The leg and top or side of the foot are involved · the patient is a female aged 50–59 · the photograph is a close-up of the affected area: 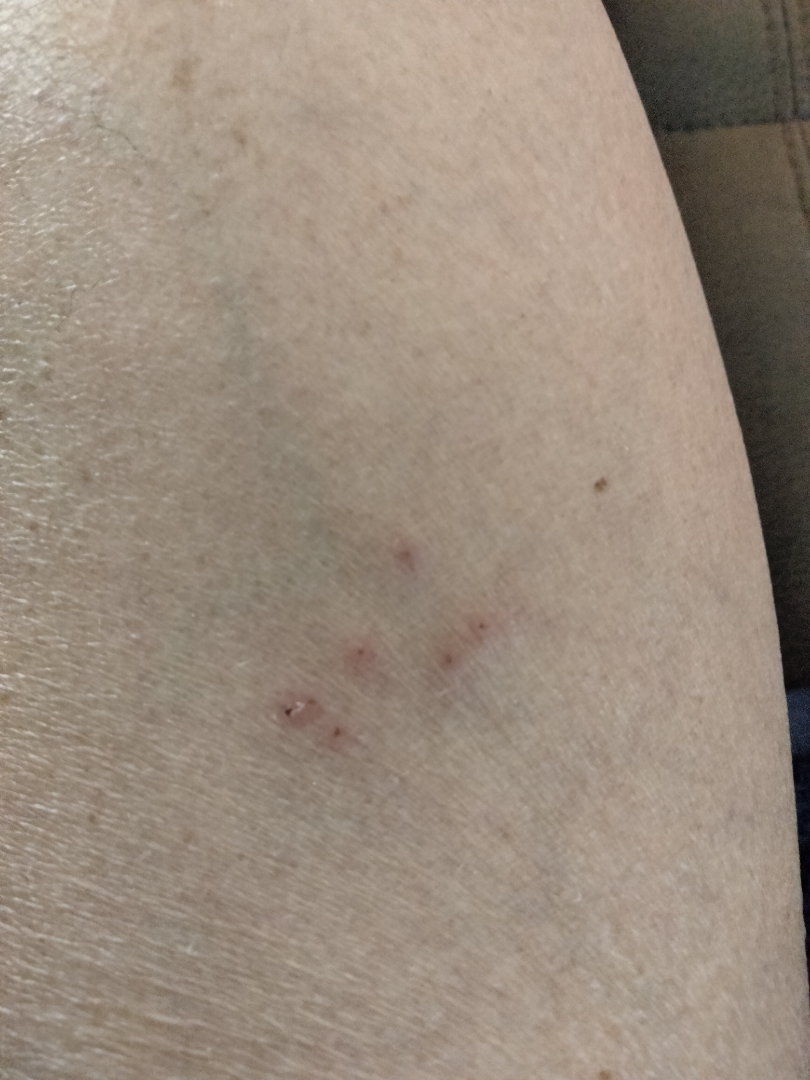The skin findings could not be characterized from the image. The lesion is described as raised or bumpy. Skin tone: Fitzpatrick IV. The patient reports itching. The patient reports the condition has been present for one to four weeks. The patient reported no systemic symptoms.